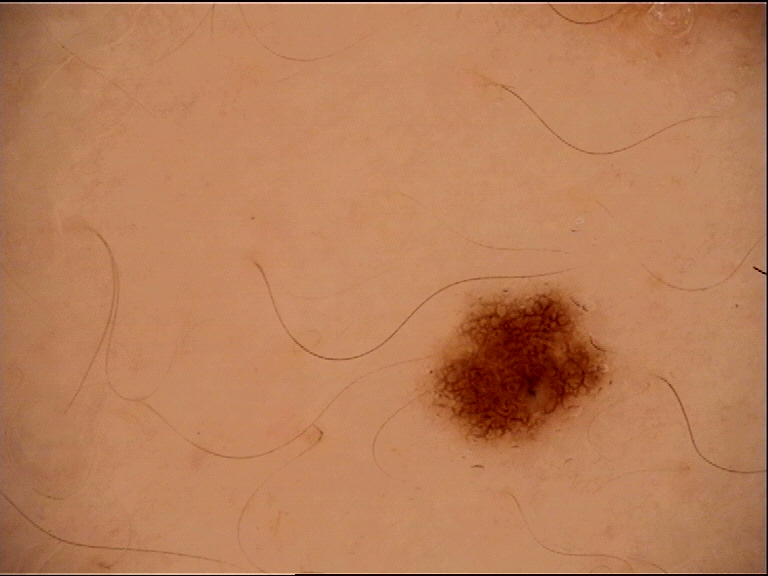Q: What kind of image is this?
A: dermatoscopy
Q: What is the diagnosis?
A: dysplastic junctional nevus (expert consensus)